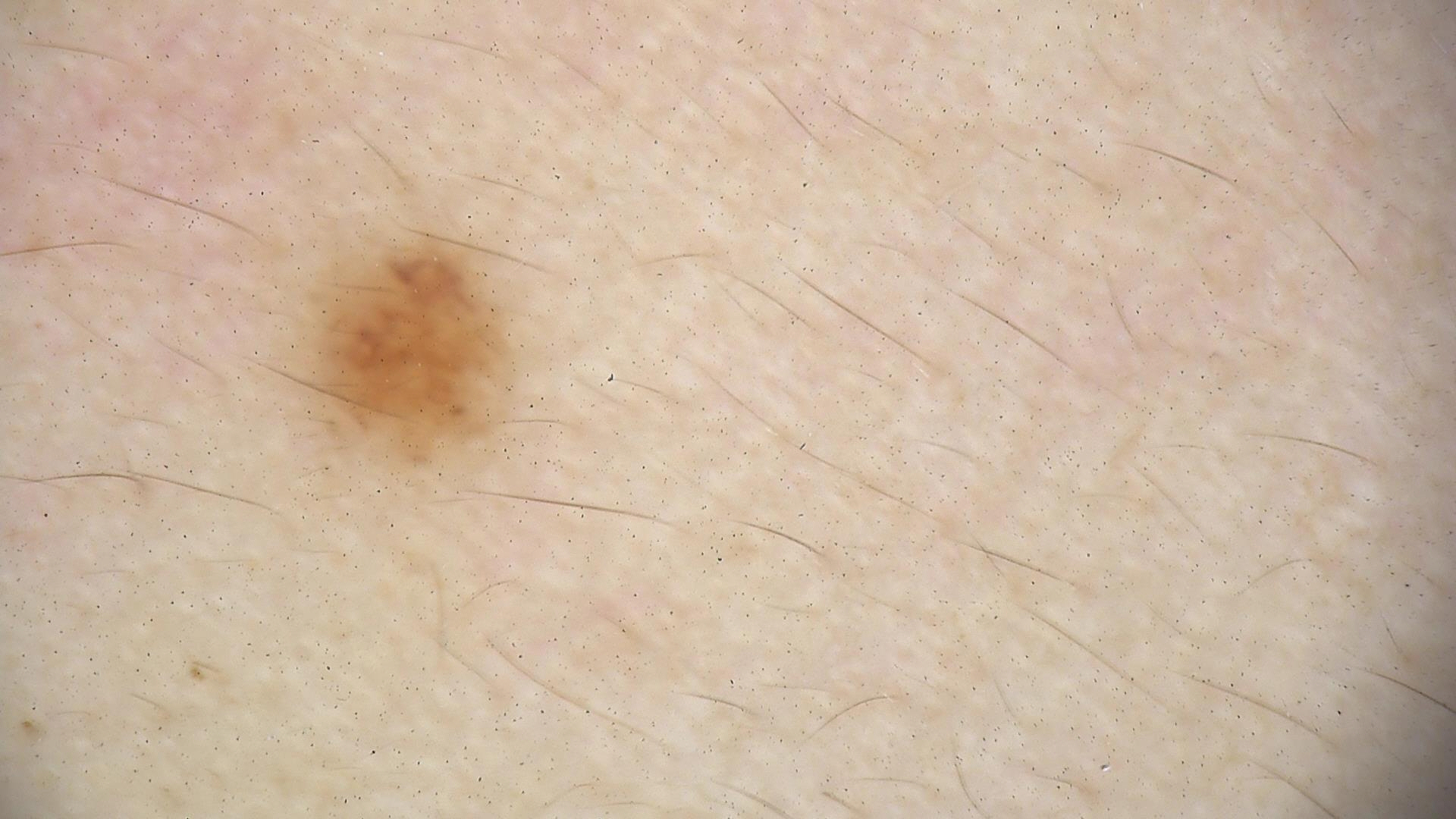Labeled as a dysplastic junctional nevus.